Skin tone: Fitzpatrick skin type IV; lay graders estimated Monk Skin Tone 5 (US pool) or 3 (India pool), symptoms reported: burning and itching, located on the leg, the condition has been present for more than one year, self-categorized by the patient as a rash, a close-up photograph: 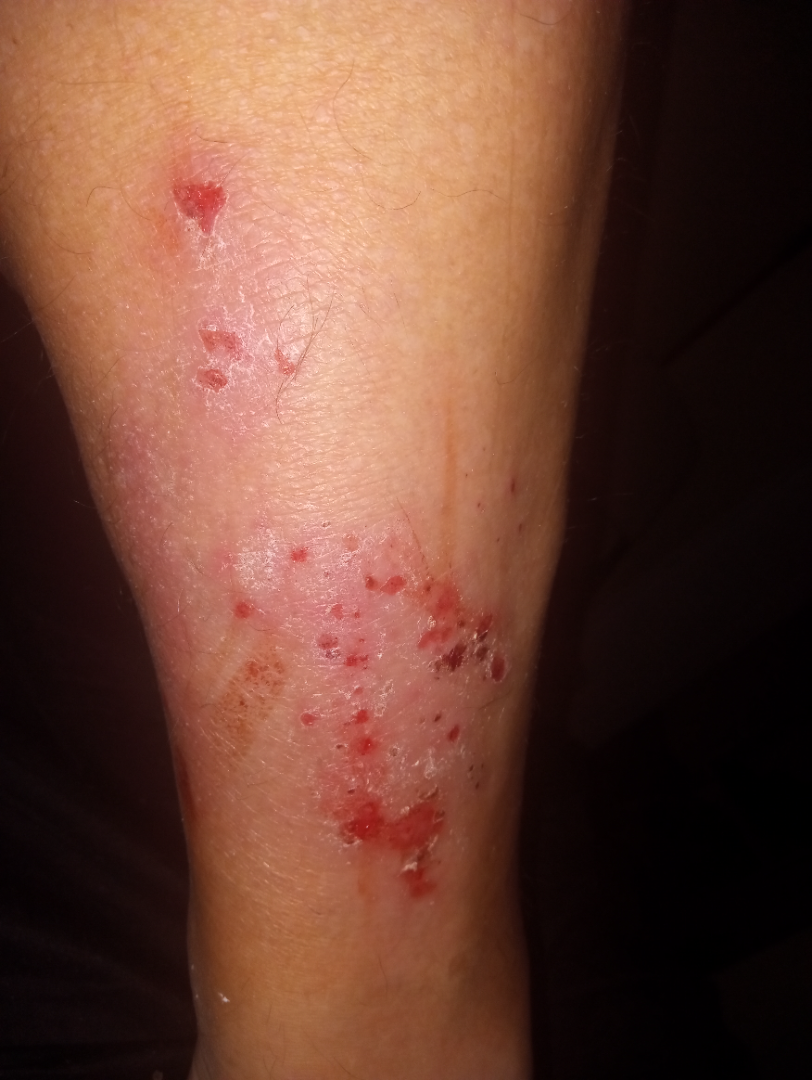impression = one reviewing dermatologist: most consistent with Lichen Simplex Chronicus; an alternative is Lichen planus/lichenoid eruption